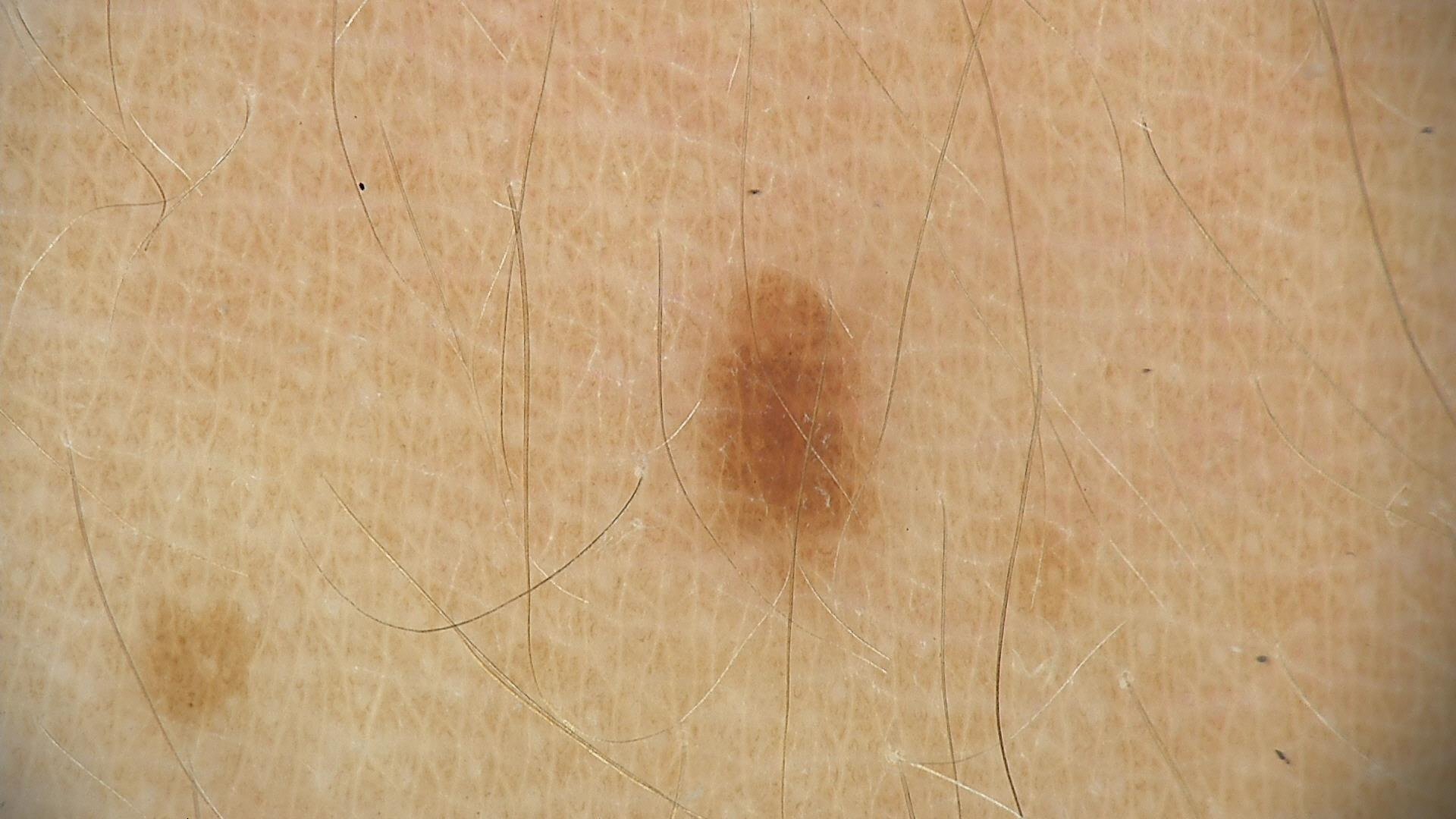Dermoscopy of a skin lesion. Classified as a dysplastic junctional nevus.